The lesion involves the leg; the contributor is a male aged 30–39; an image taken at a distance.
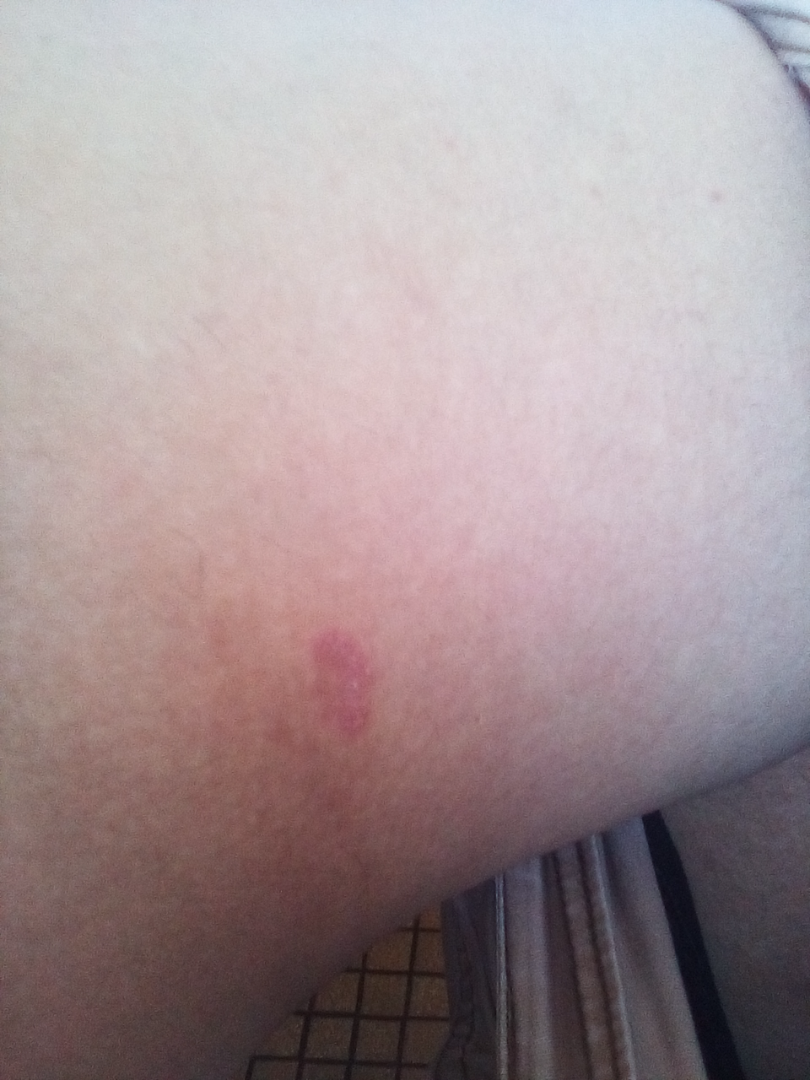differential diagnosis: Tinea and Eczema were considered with similar weight